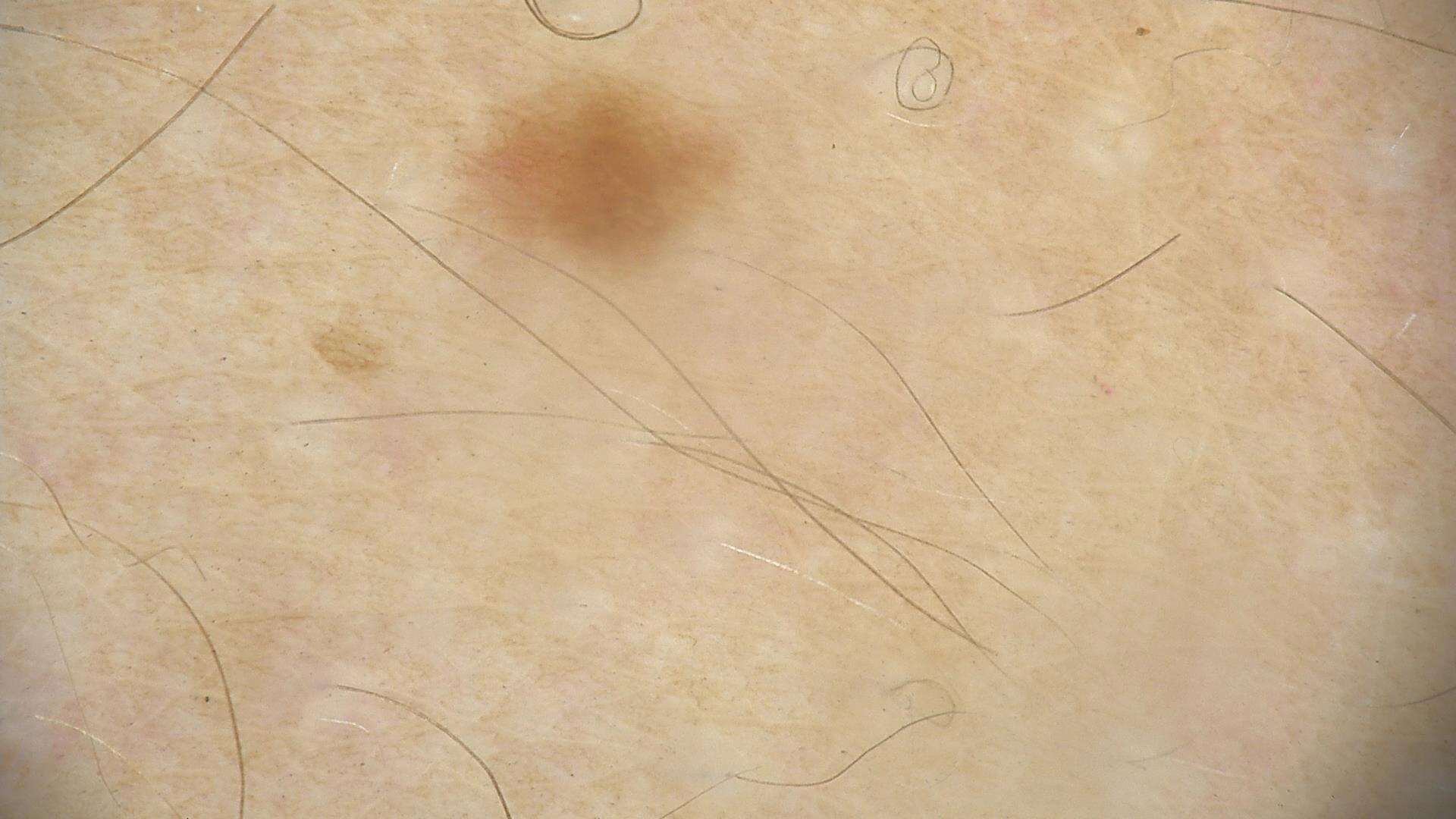Labeled as a benign lesion — a dysplastic junctional nevus.